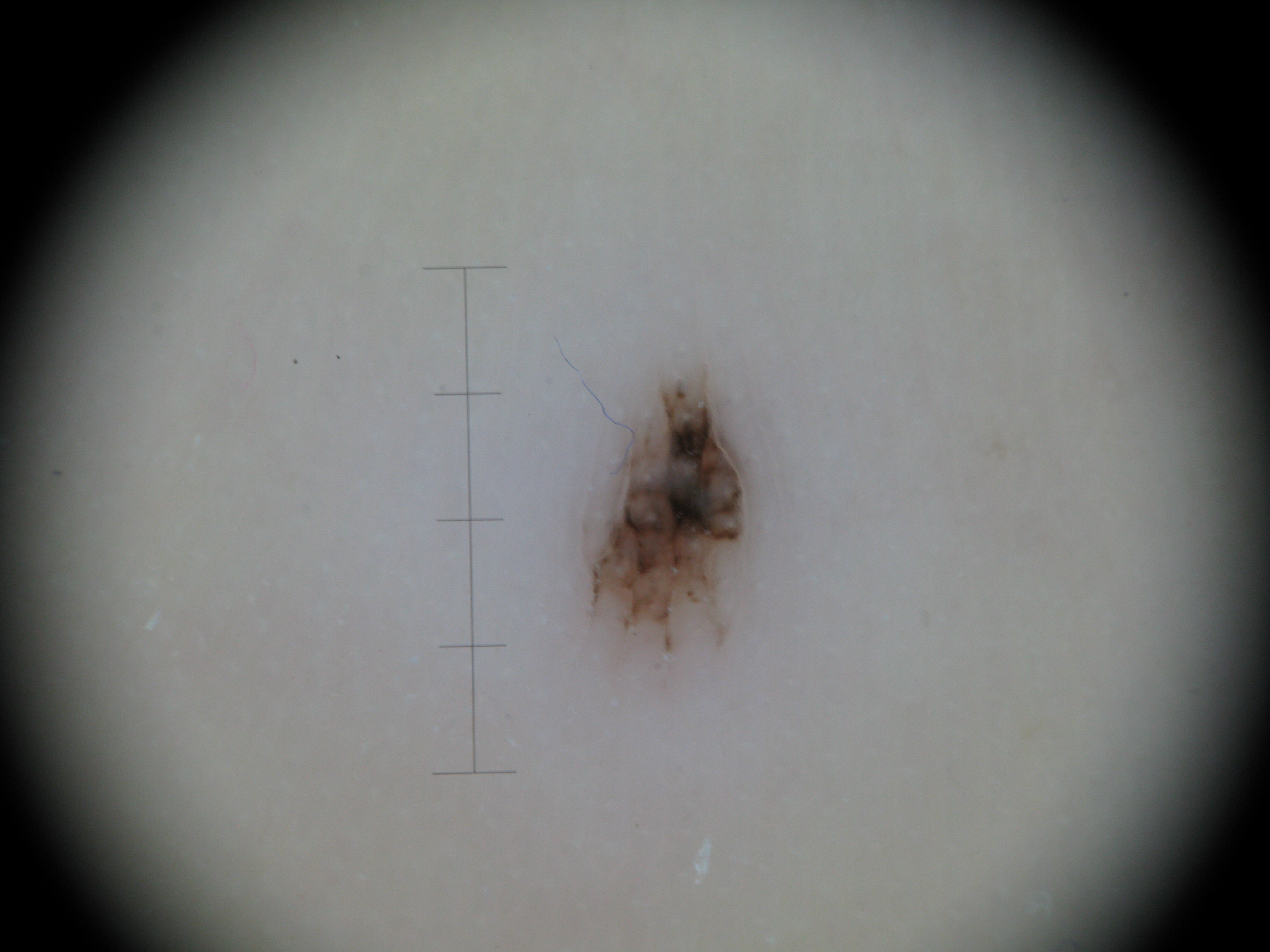Case:
• imaging · dermatoscopy
• subtype · banal
• label · acral compound nevus (expert consensus)